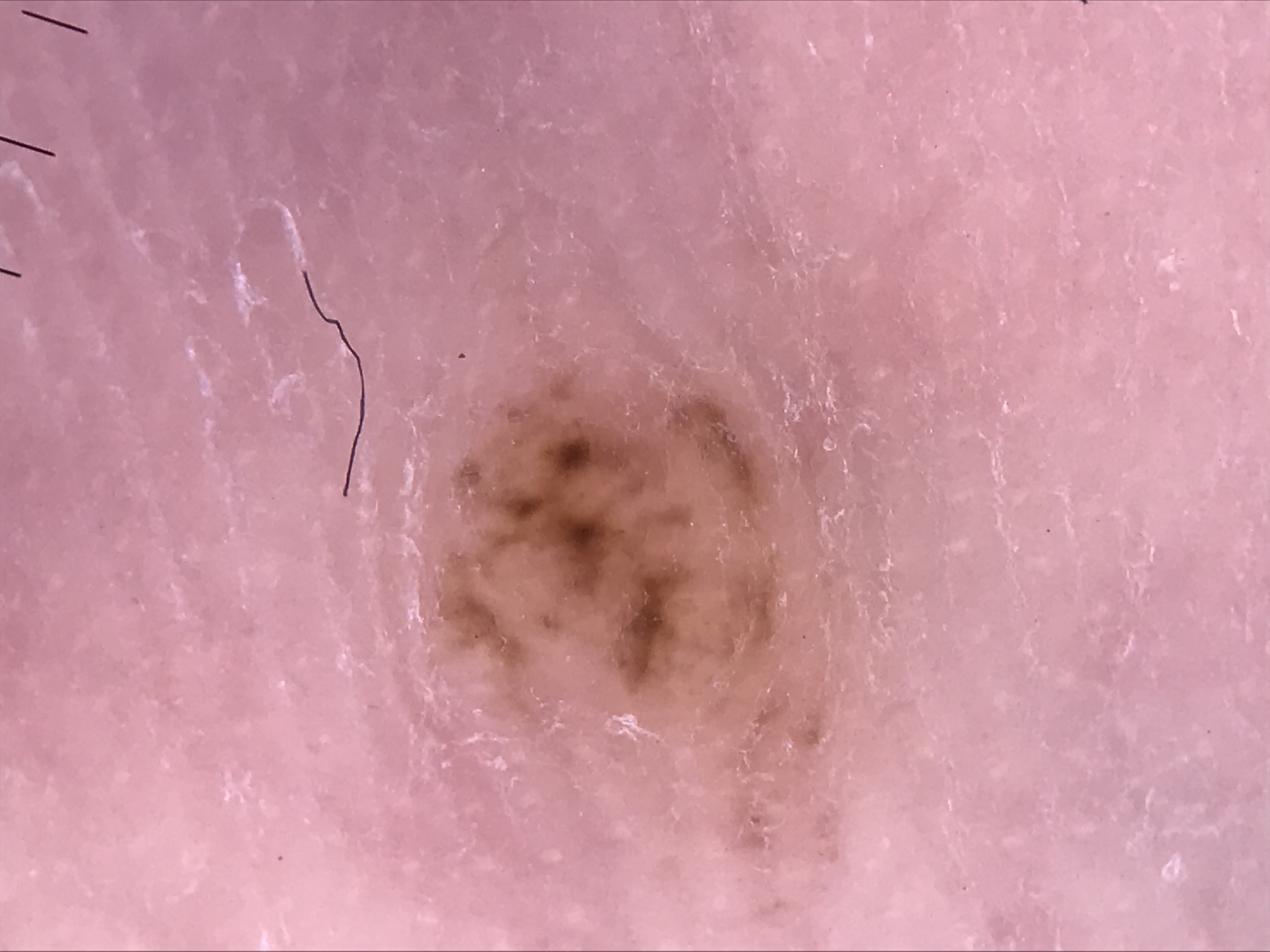A dermoscopic image of a skin lesion. The diagnostic label was a banal lesion — an acral compound nevus.